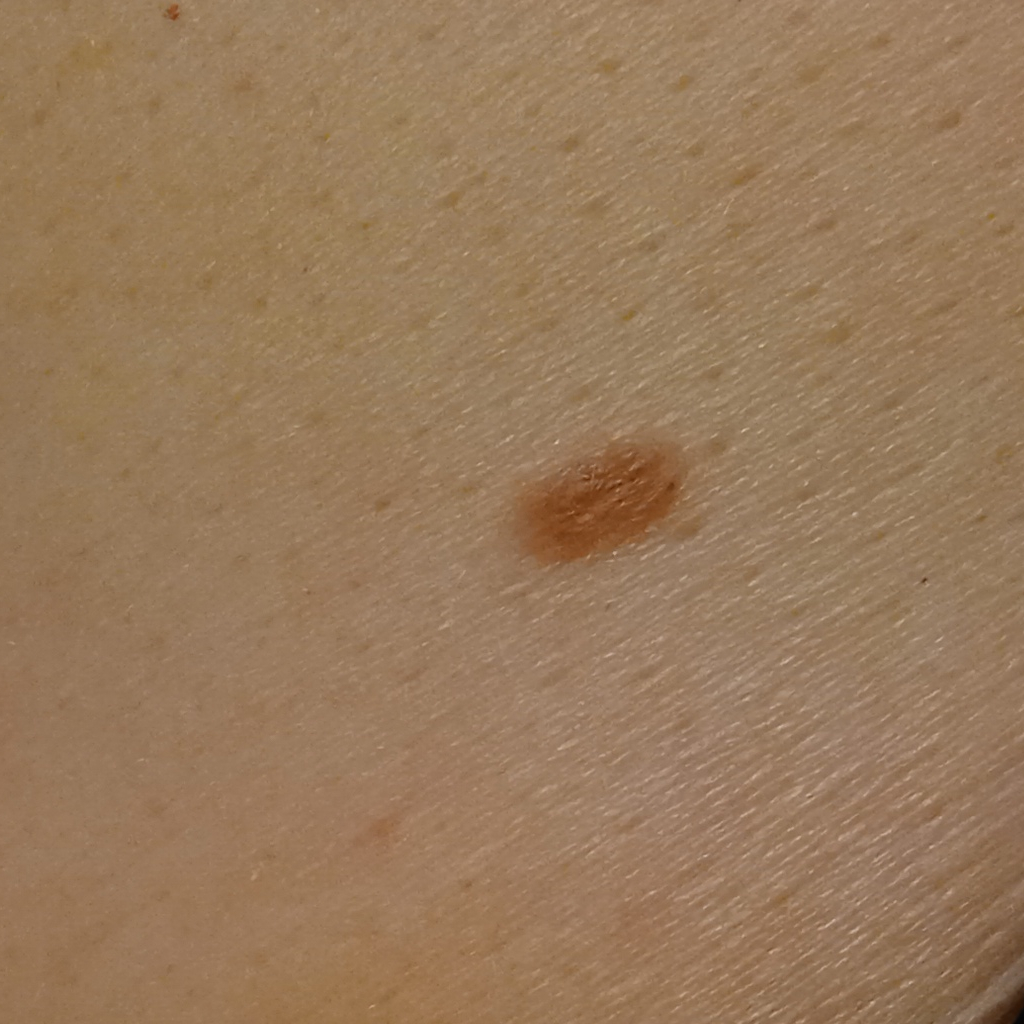subject: female, 50 years of age
nevus count: a moderate number of melanocytic nevi
referral context: research study (no referral diagnosis)
anatomic site: the torso
diagnostic label: melanocytic nevus (dermatologist consensus)